A male subject 51 years of age.
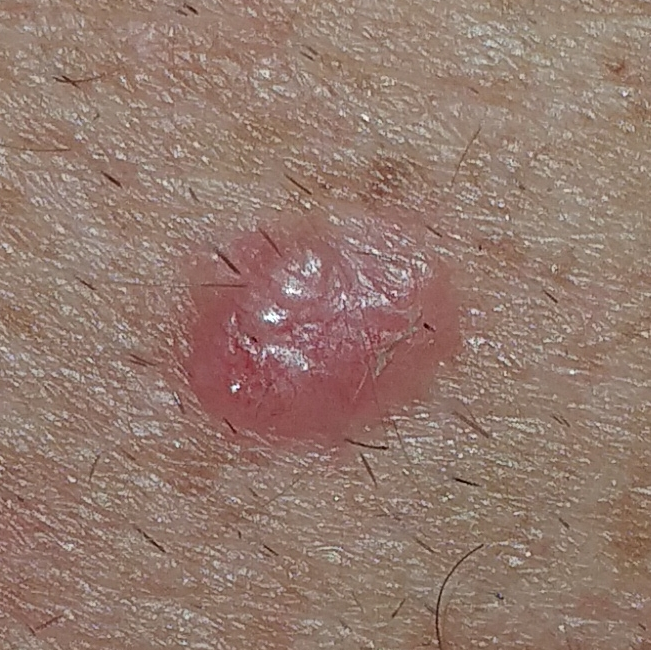The lesion involves the back.
Biopsy-confirmed as a basal cell carcinoma.